A dermoscopy image of a single skin lesion:
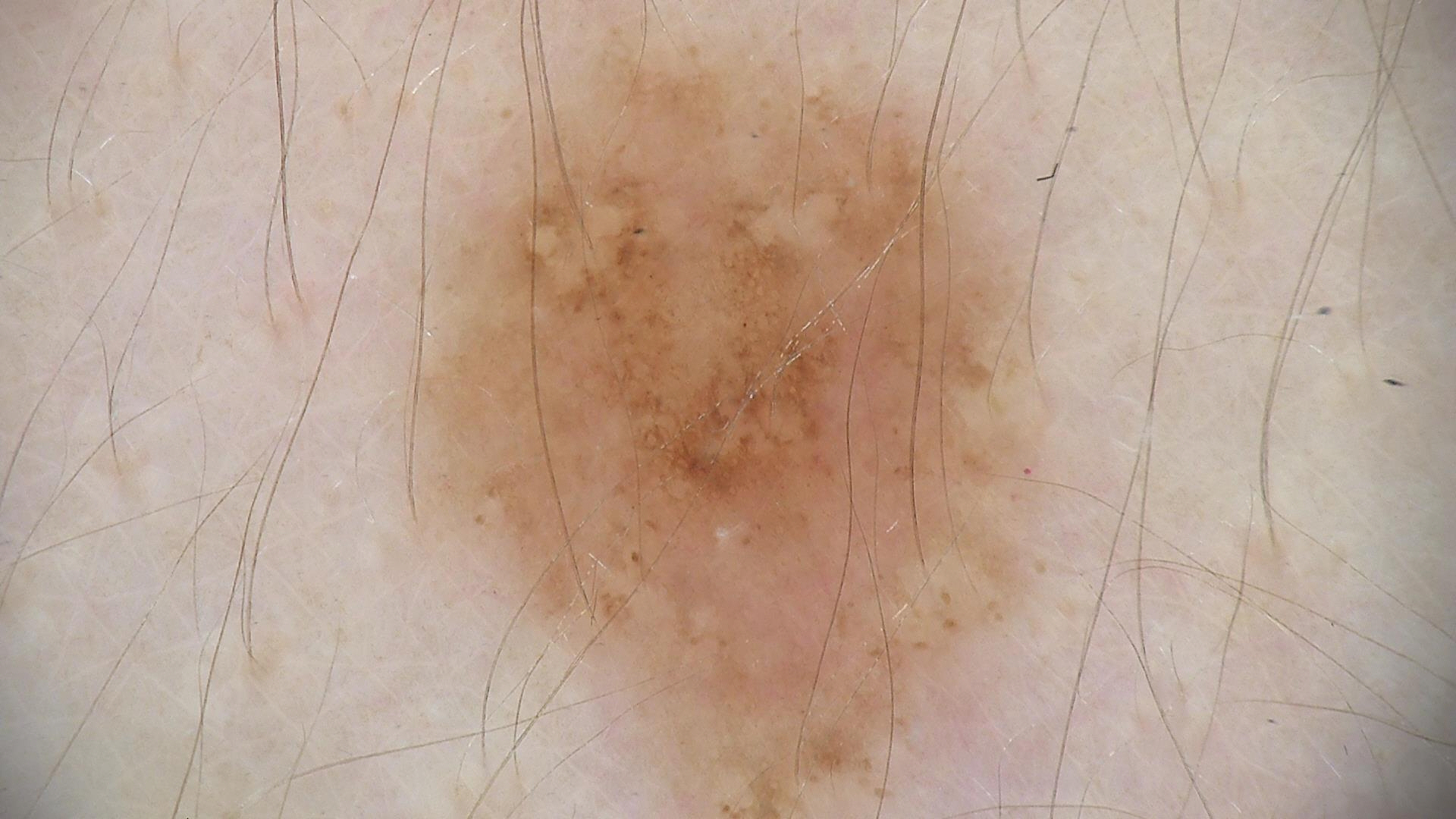{"diagnosis": {"name": "dysplastic junctional nevus", "code": "jd", "malignancy": "benign", "super_class": "melanocytic", "confirmation": "expert consensus"}}